The patient describes having few moles overall · a clinical photograph of a skin lesion · the patient says their skin reddens with sun exposure · collected as part of a research study, without a referral diagnosis — 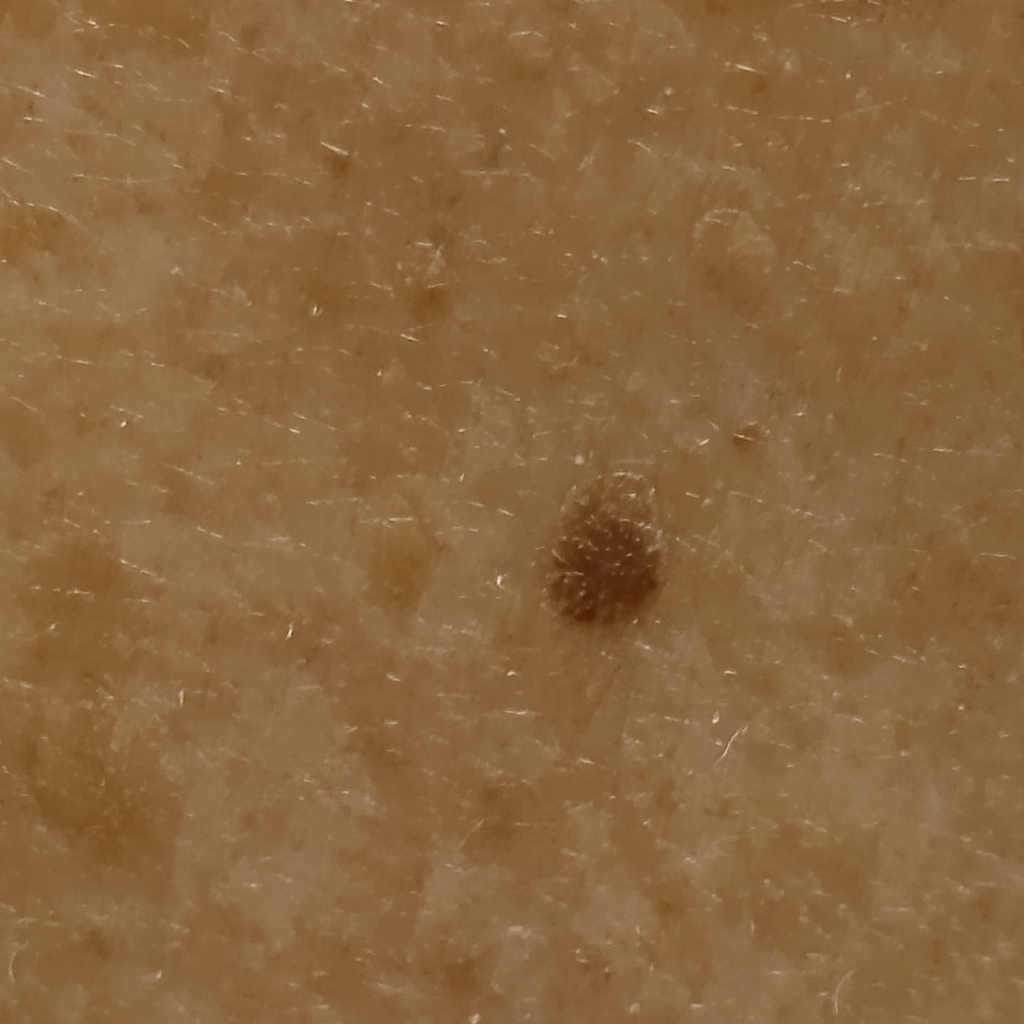Case summary:
The lesion measures approximately 4.3 mm.
Impression:
The lesion was assessed as a seborrheic keratosis.